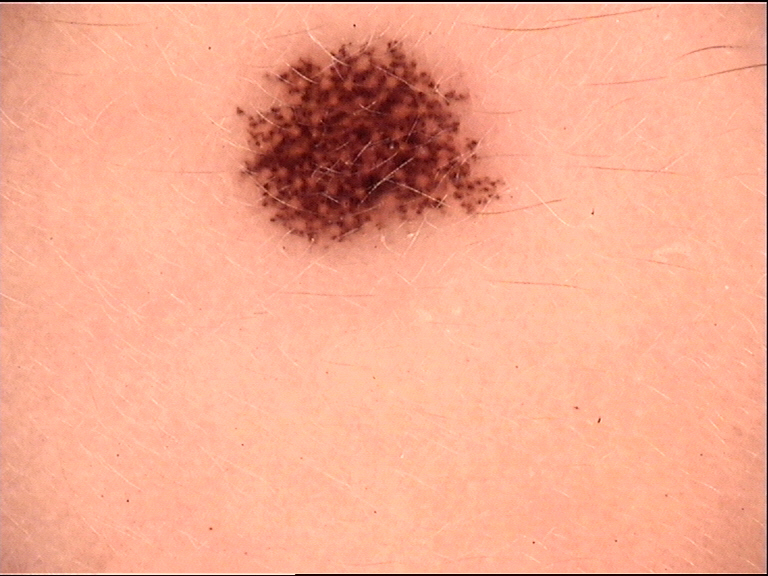• diagnostic label — dysplastic junctional nevus (expert consensus)